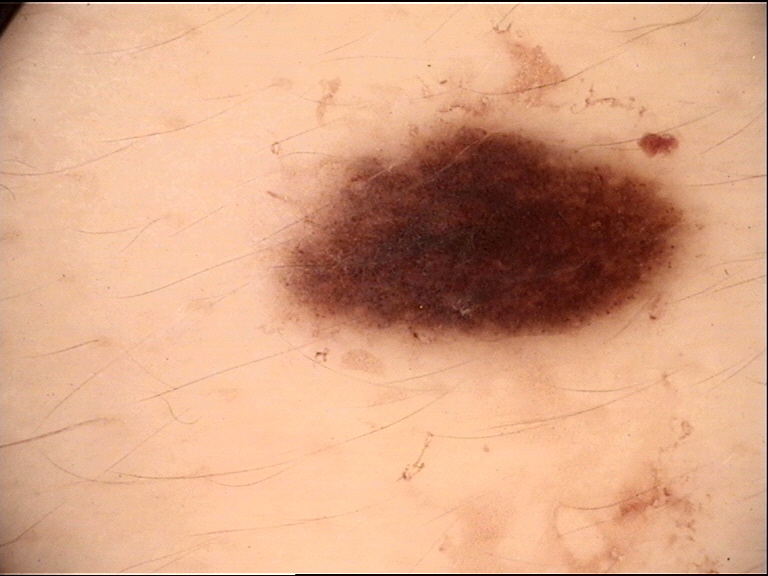{
  "diagnosis": {
    "name": "dysplastic junctional nevus",
    "code": "jd",
    "malignancy": "benign",
    "super_class": "melanocytic",
    "confirmation": "expert consensus"
  }
}